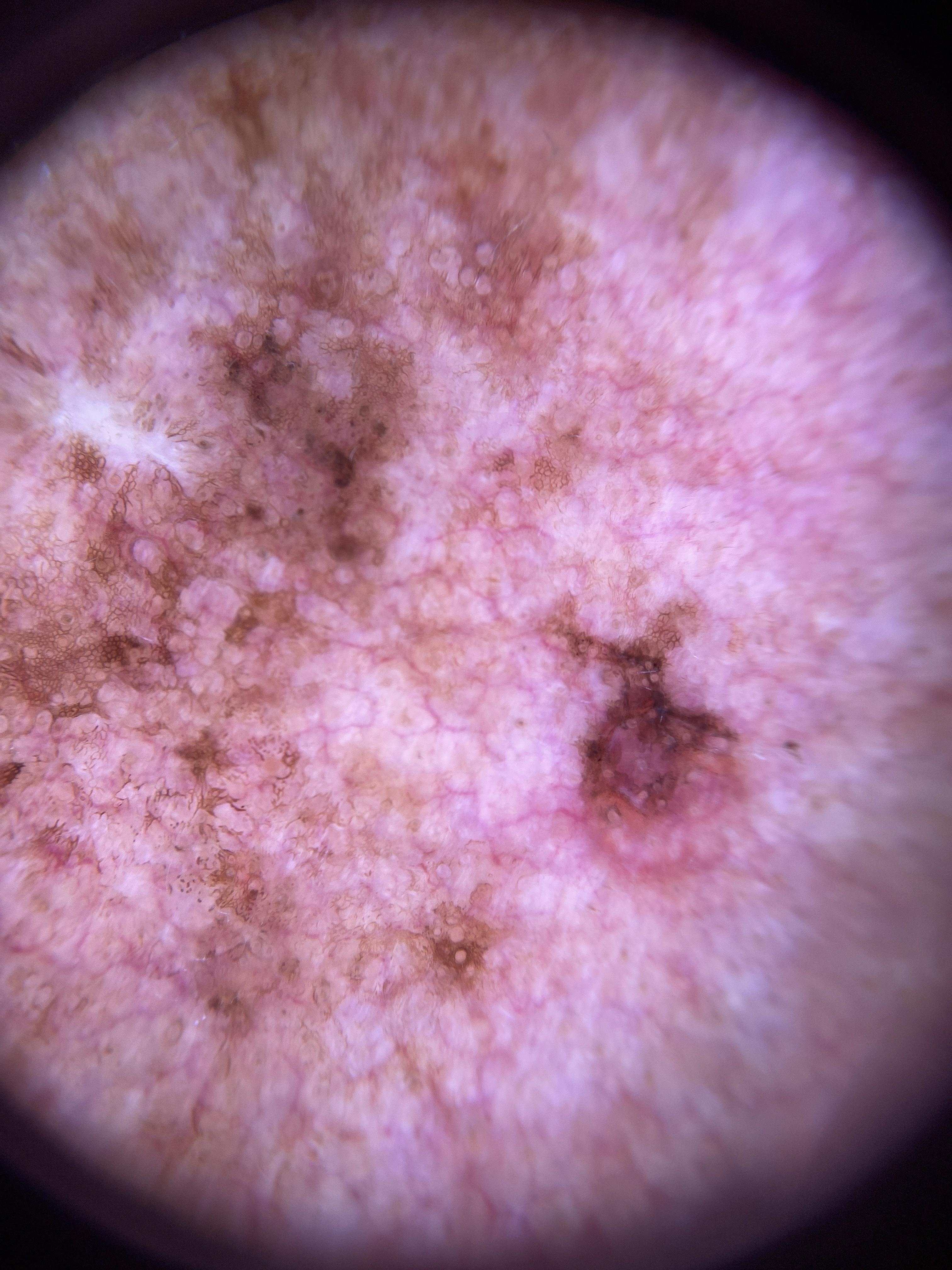Pathology: Biopsy-confirmed as a melanoma.